By self-report, a personal history of skin cancer and a personal history of cancer. A skin lesion imaged with a dermatoscope. The patient says their skin tans without first burning. Imaged for a research study, with no referral diagnosis recorded. A female patient age 60. Few moles overall by the patient's own estimate — 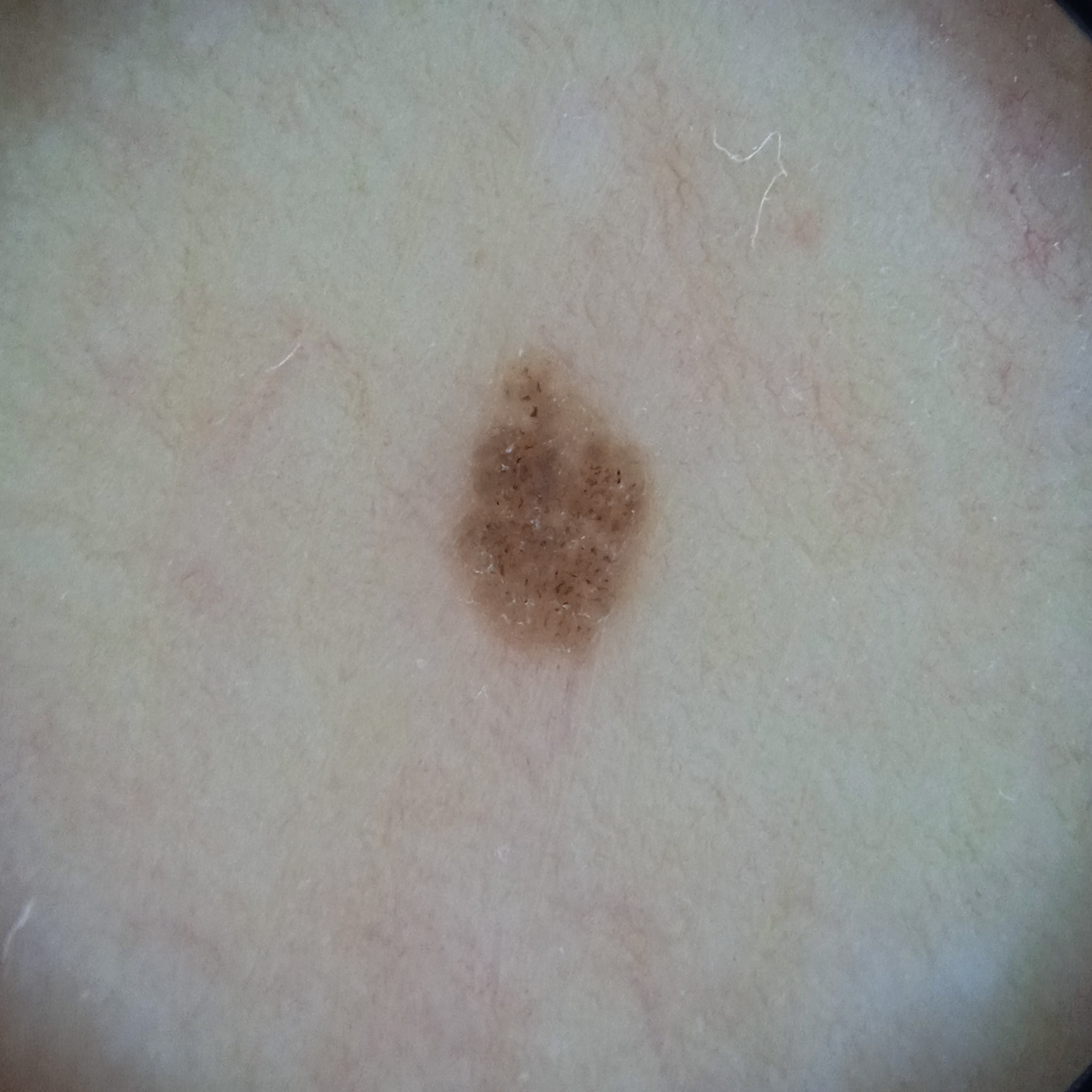Q: Where is the lesion?
A: the torso
Q: How large is the lesion?
A: 3.4 mm
Q: What was the diagnosis?
A: melanocytic nevus (dermatologist consensus)